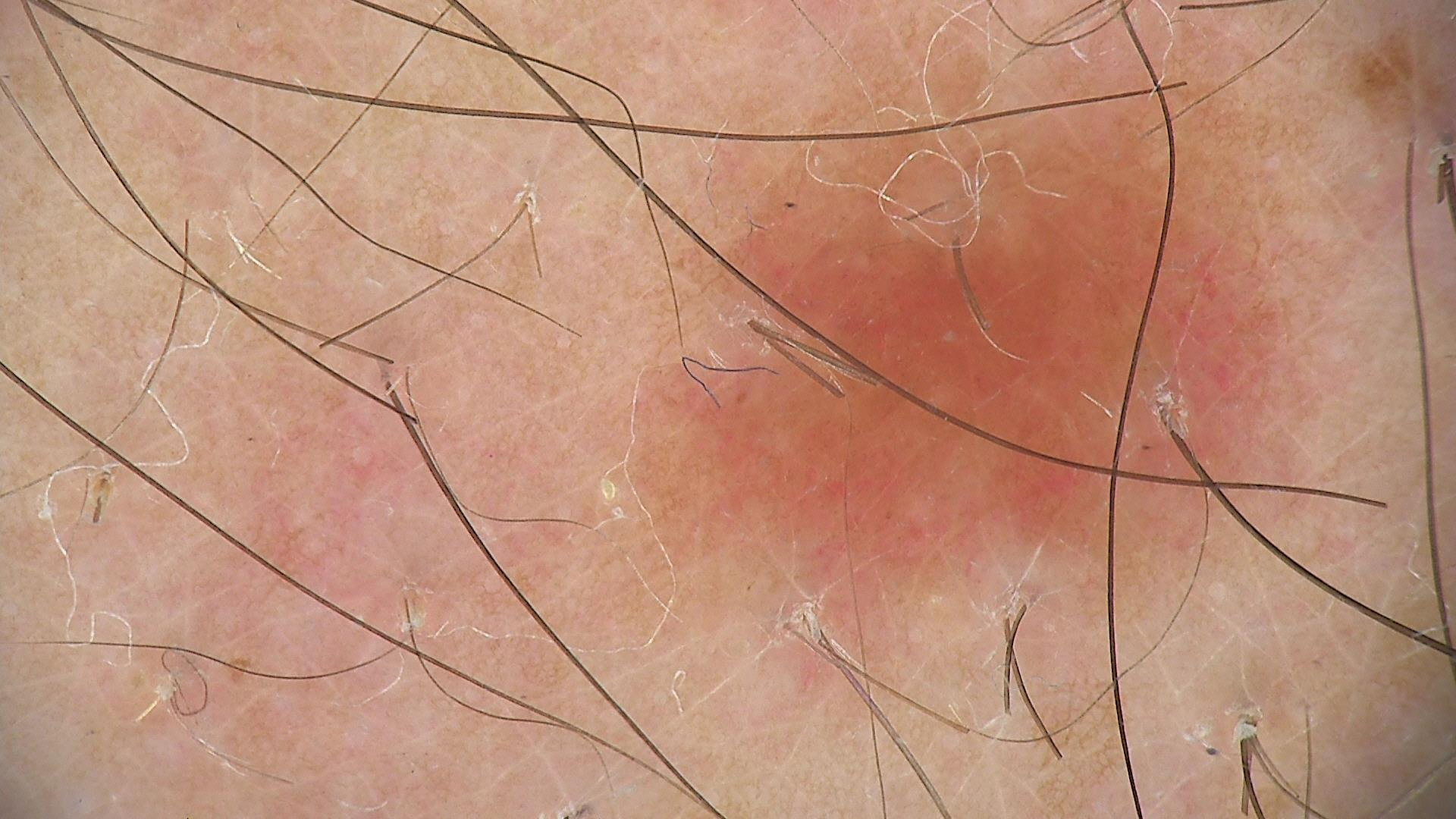The diagnosis was a benign lesion — a dysplastic junctional nevus.